A clinical close-up photograph of a skin lesion:
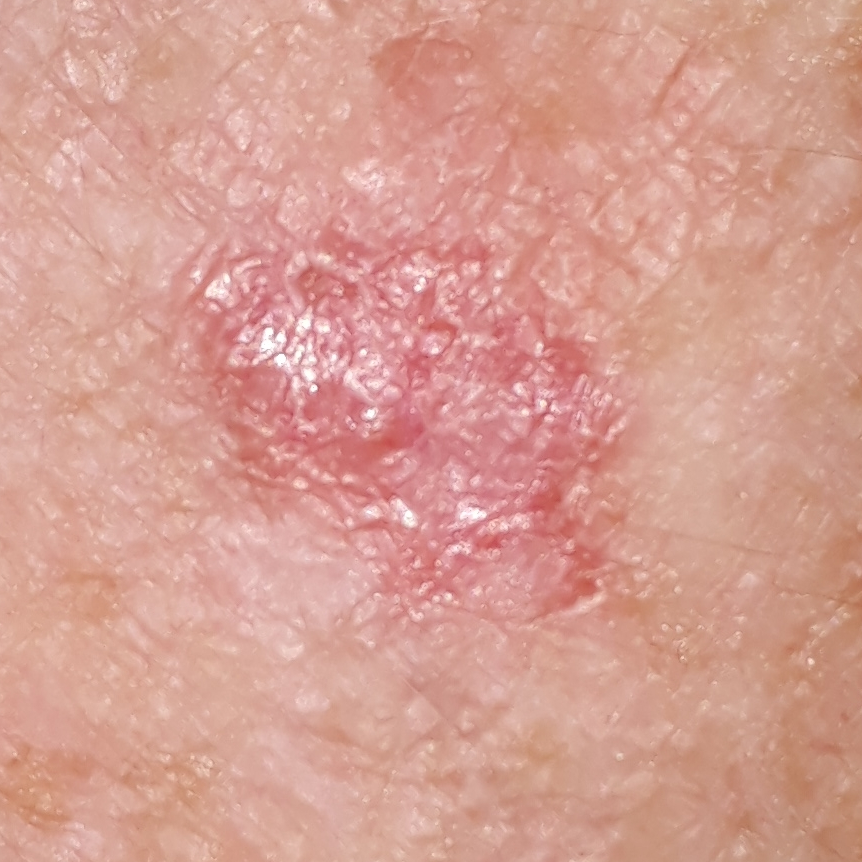Clinical context: By the patient's account, the lesion is elevated and itches. Conclusion: Biopsy-confirmed as a basal cell carcinoma.